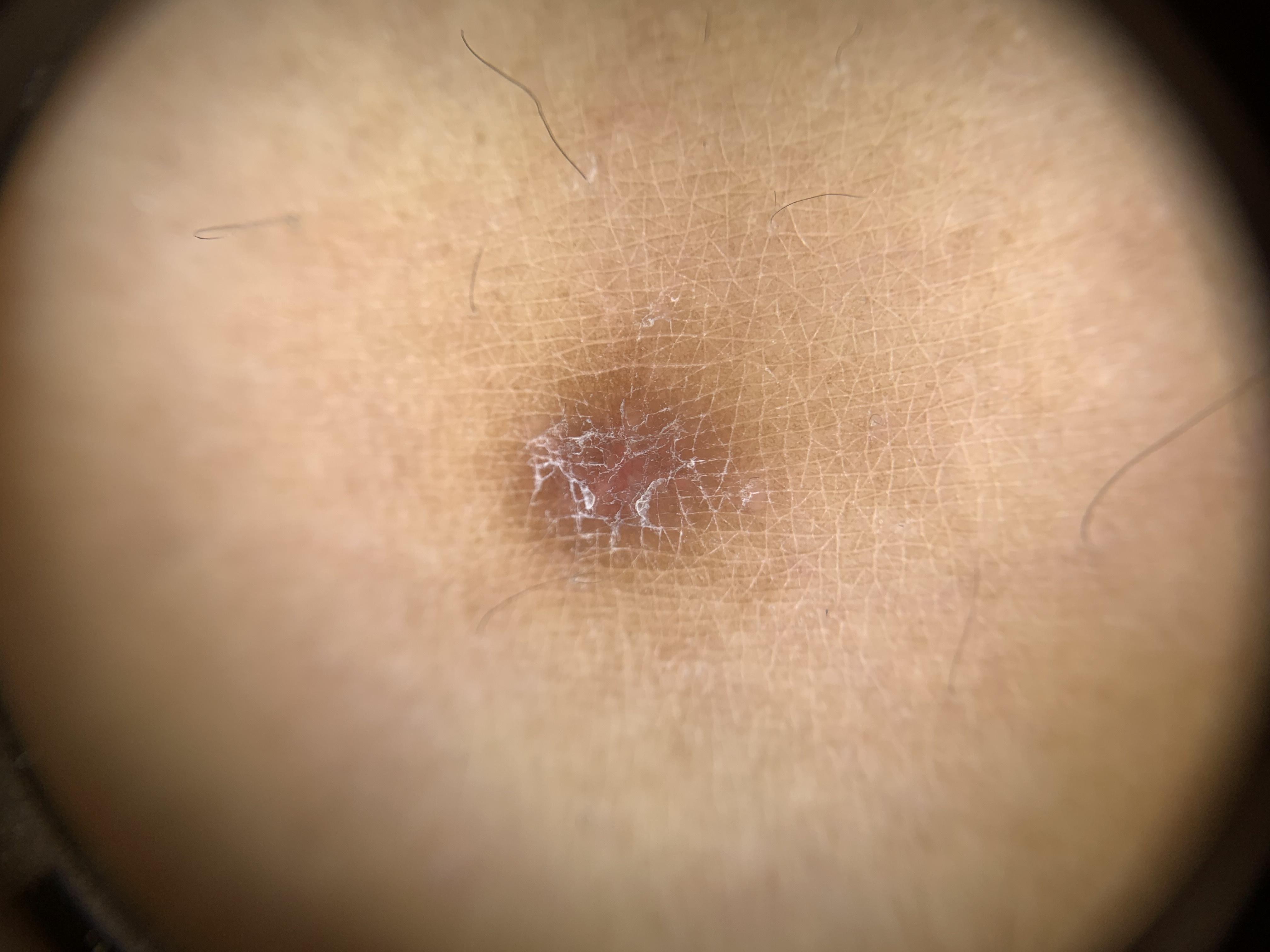A dermatoscopic image of a skin lesion.
A female subject about 45 years old.
Recorded as skin type II.
Located on a lower extremity.
The clinical assessment was a dermatofibroma.